A female subject approximately 75 years of age. A clinical overview photograph of a skin lesion. Fitzpatrick phototype II. The chart documents melanoma in a first-degree relative.
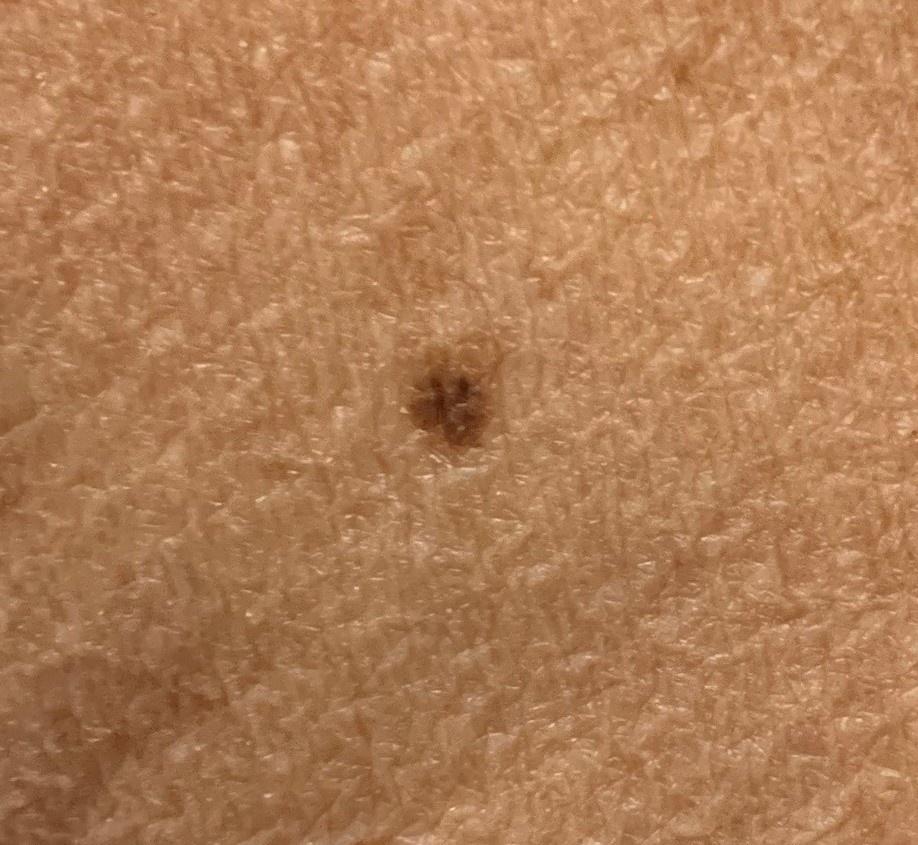Image and clinical context: The lesion was found on an upper extremity. Conclusion: Consistent with a melanocytic lesion — a nevus.